A male subject 83 years old; a smartphone photograph of a skin lesion; the chart records prior skin cancer (patient or family) and alcohol use; the patient was assessed as Fitzpatrick skin type II:
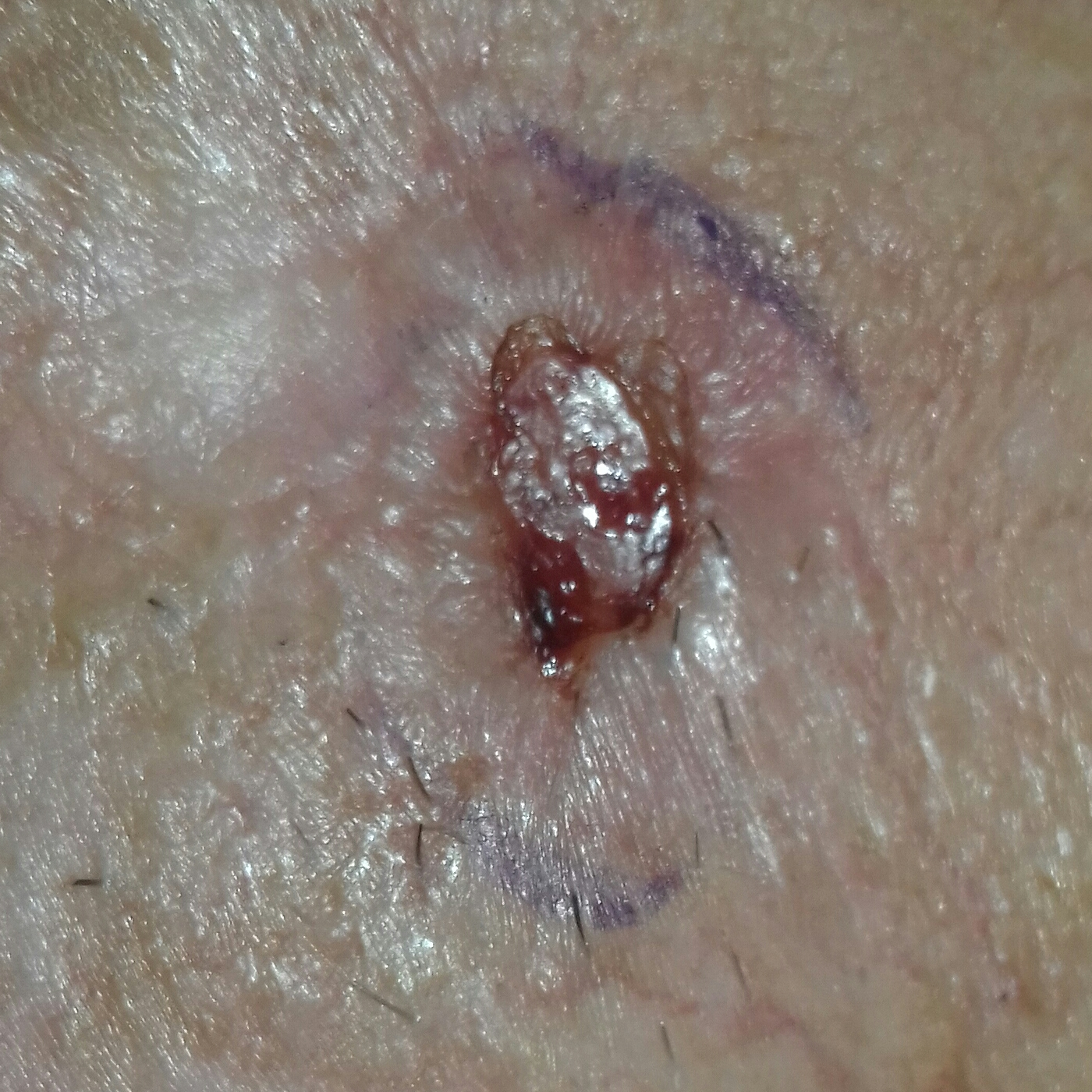Case summary:
The lesion is roughly 11 by 9 mm. The patient reports that the lesion has grown, has bled, itches, and hurts, but is not elevated and has not changed.
Pathology:
Biopsy-confirmed as a basal cell carcinoma.